A female subject 81 years old. A dermoscopic image of a skin lesion. Collected as part of a research study, without a referral diagnosis. The patient says their skin reddens painfully with sun exposure. The patient describes having a moderate number of moles:
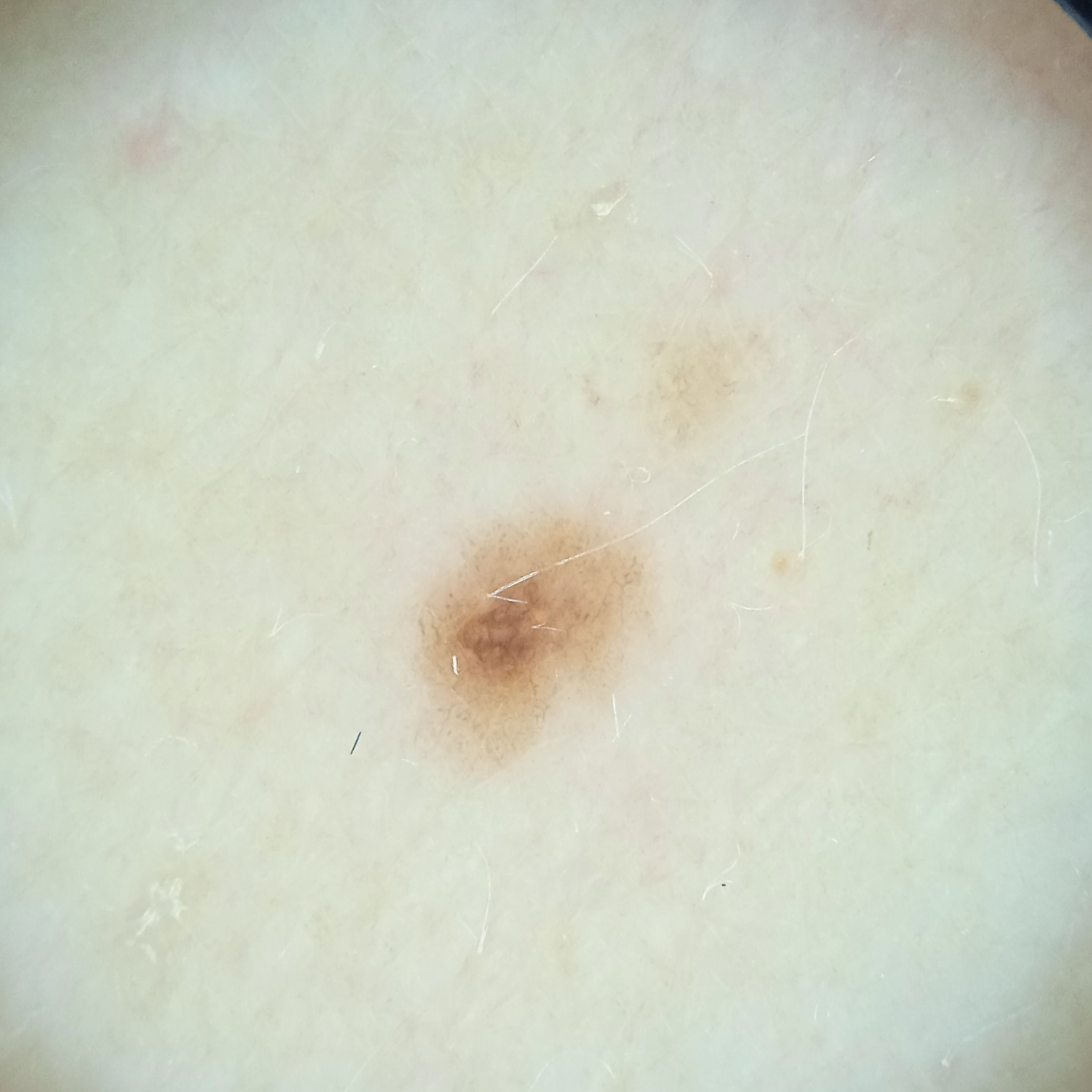| feature | finding |
|---|---|
| site | the back |
| diameter | 2.7 mm |
| diagnosis | melanocytic nevus (dermatologist consensus) |